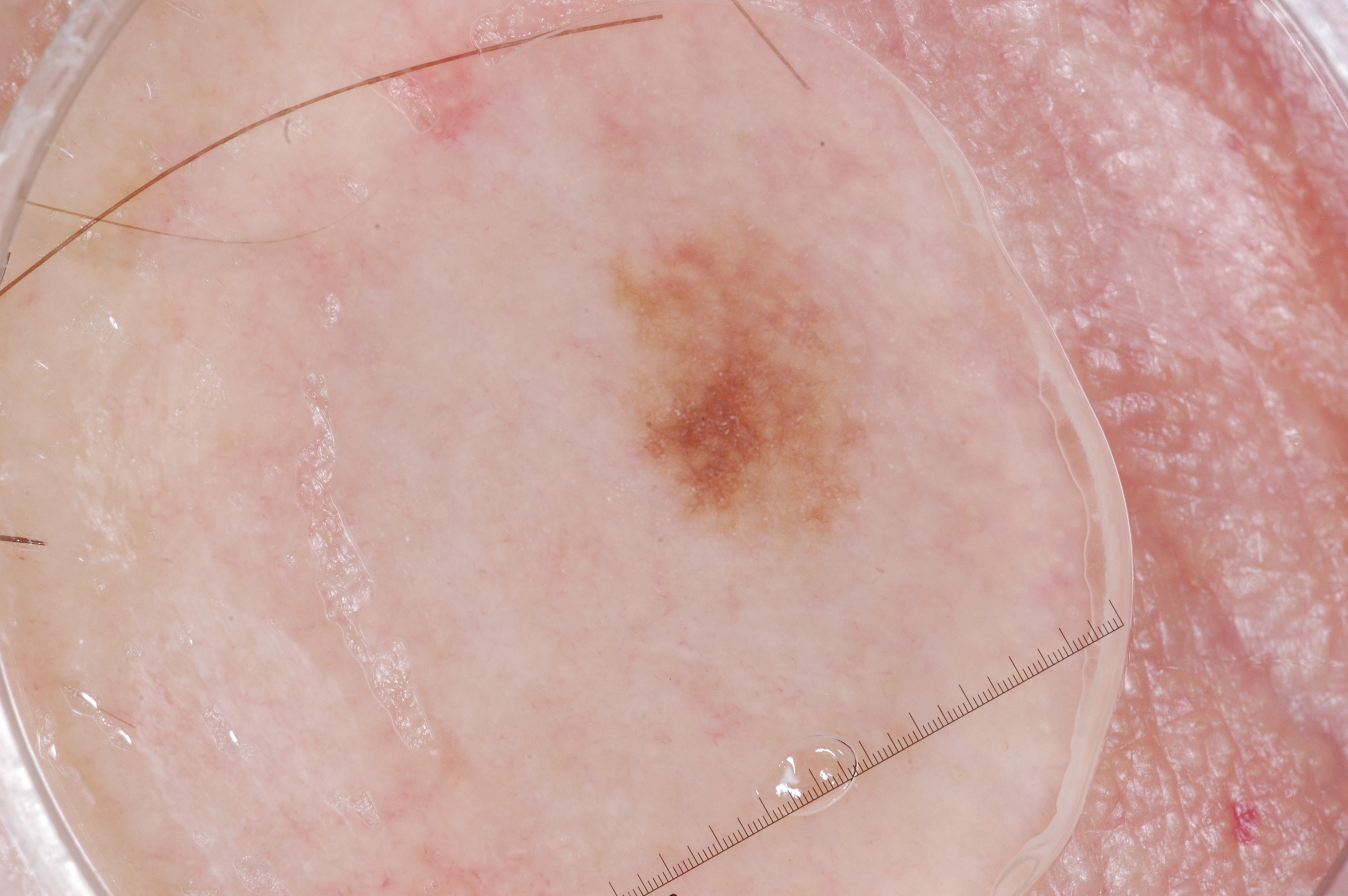• subject · male, aged approximately 55
• modality · dermatoscopic image of a skin lesion
• size · small
• dermoscopic features · pigment network
• lesion bbox · <box>591, 202, 885, 563</box>
• diagnostic label · a melanocytic nevus